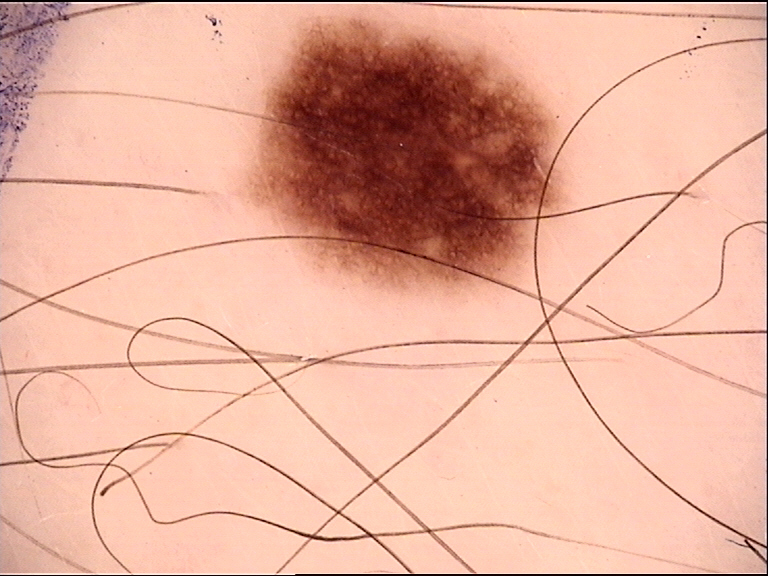Findings:
A dermoscopy image of a single skin lesion.
Conclusion:
The diagnostic label was a benign lesion — a dysplastic junctional nevus.